A skin lesion imaged with a dermatoscope.
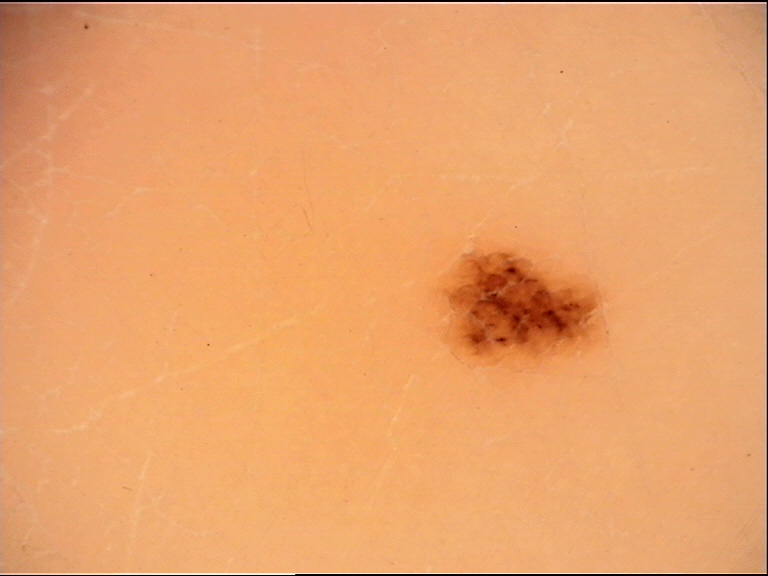Conclusion:
Diagnosed as an acral dysplastic junctional nevus.